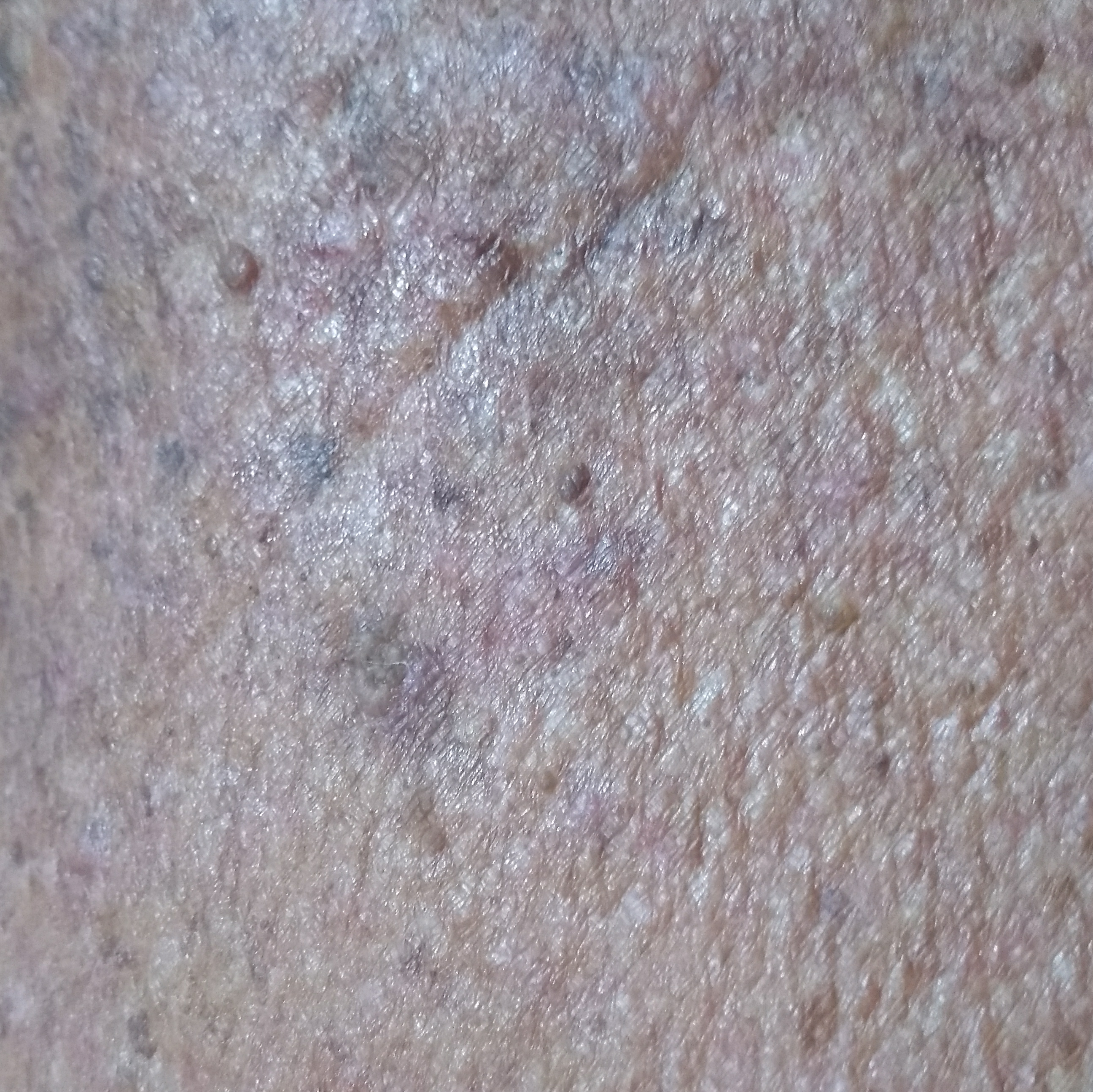Summary:
A smartphone photograph of a skin lesion. A patient in their 50s. The lesion involves an arm. The patient describes that the lesion itches, but has not bled.
Conclusion:
Consistent with a premalignant lesion — an actinic keratosis.